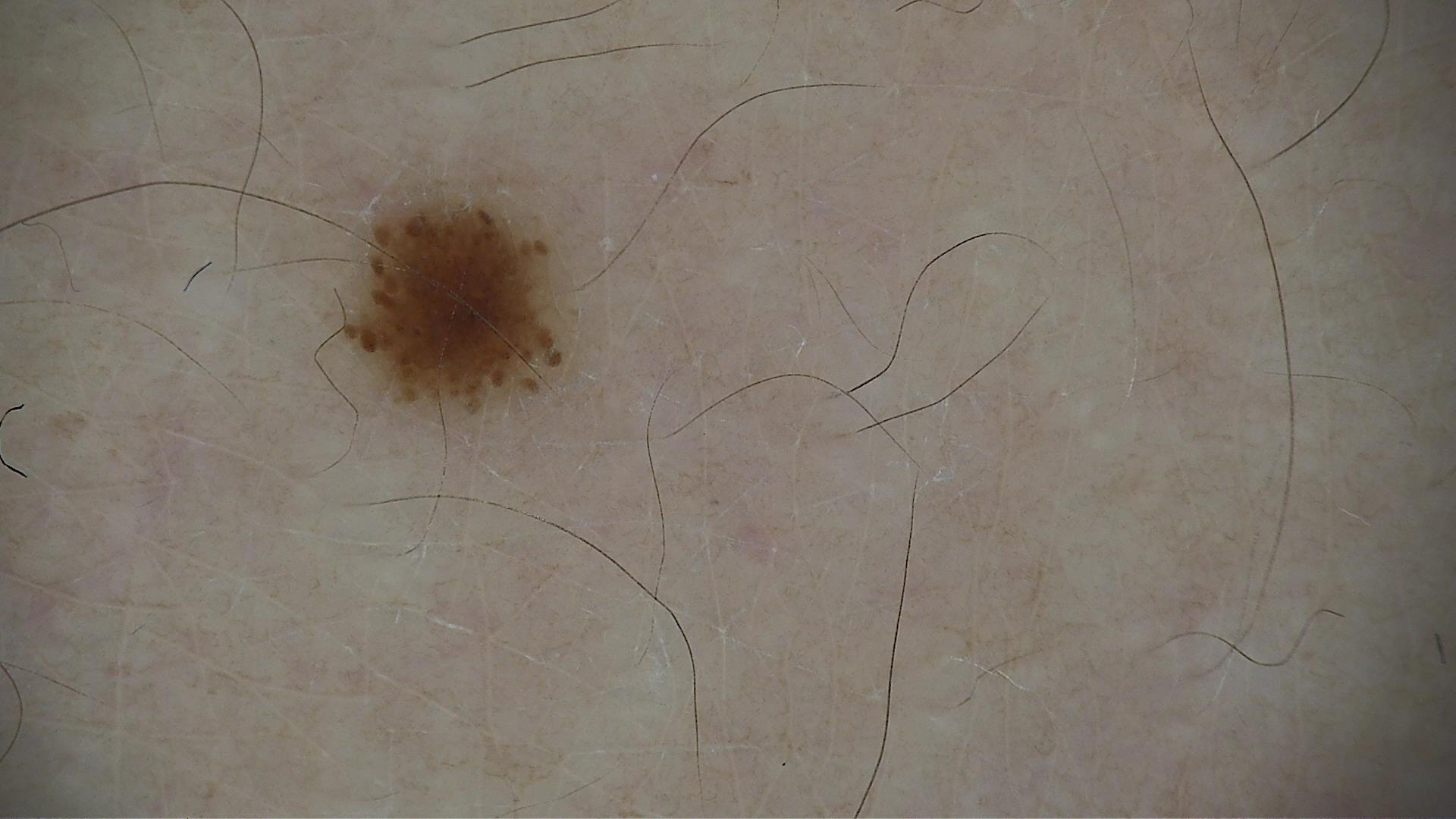Classified as a dysplastic junctional nevus.